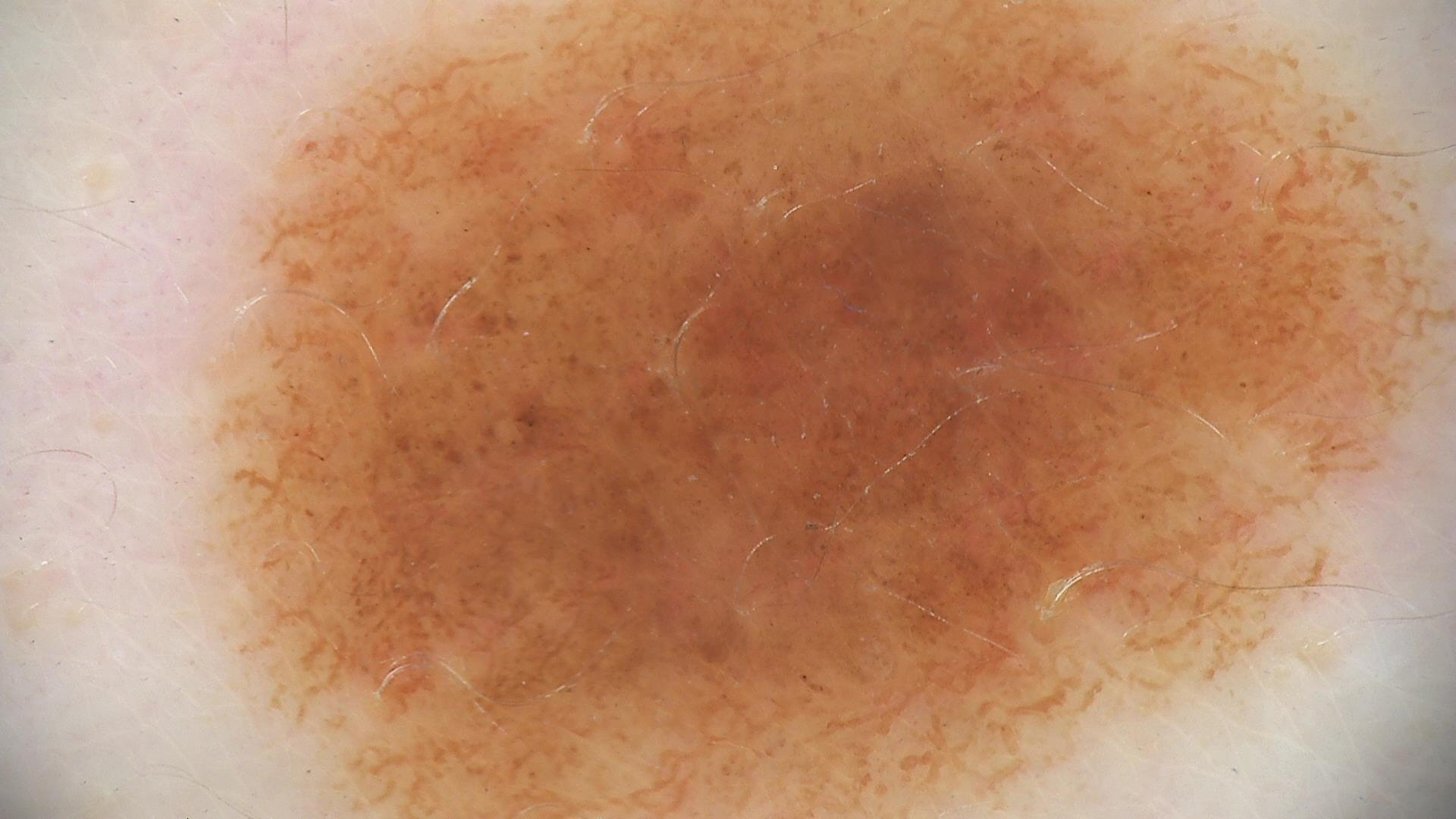Q: What kind of image is this?
A: dermatoscopy
Q: What is the diagnosis?
A: dysplastic junctional nevus (expert consensus)